Dermoscopy of a skin lesion.
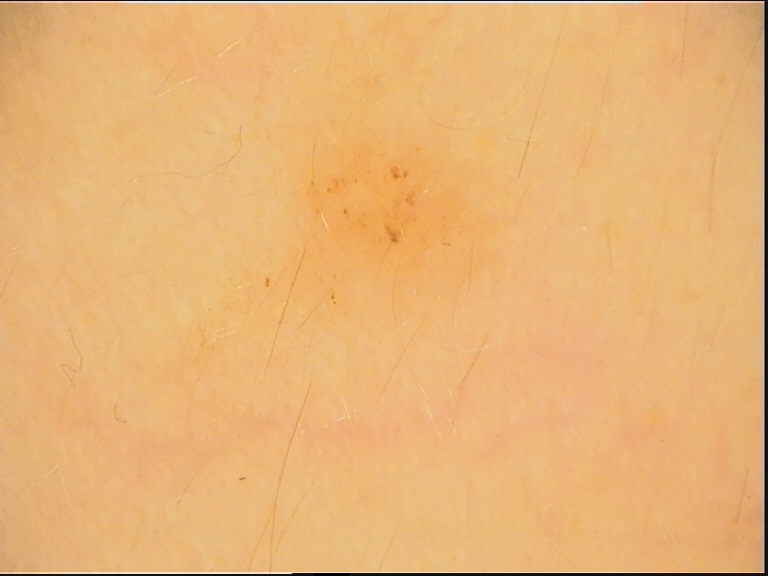diagnosis = dysplastic junctional nevus (expert consensus).